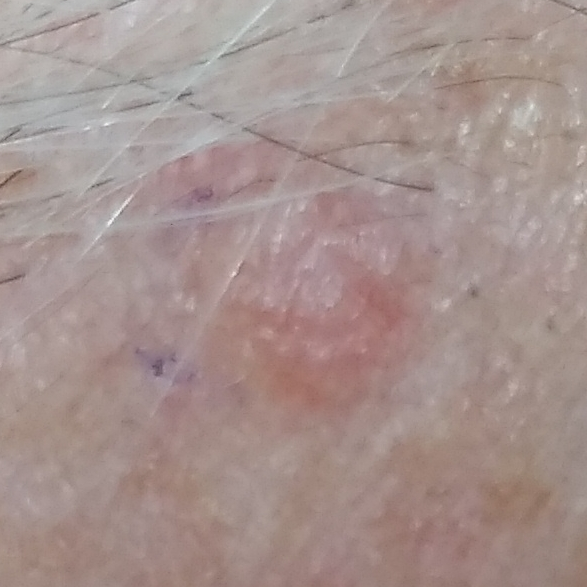On biopsy, the diagnosis was a basal cell carcinoma.